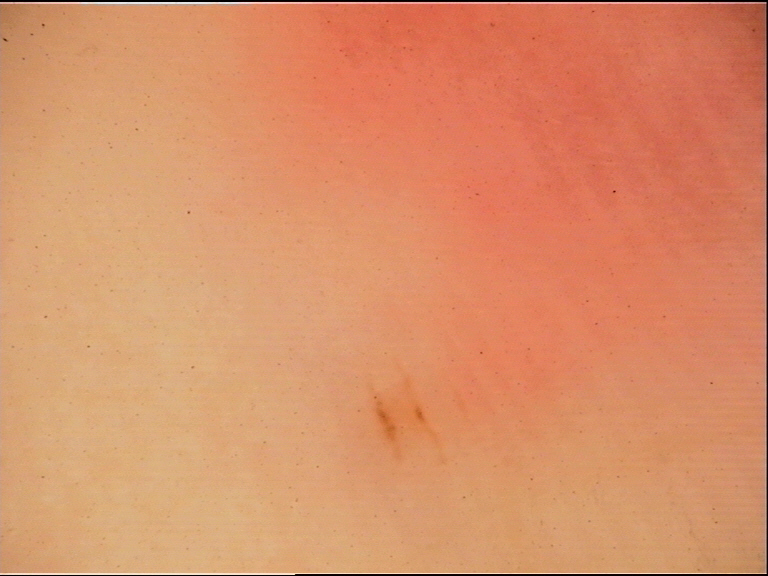{
  "diagnosis": {
    "name": "acral junctional nevus",
    "code": "ajb",
    "malignancy": "benign",
    "super_class": "melanocytic",
    "confirmation": "expert consensus"
  }
}